No associated systemic symptoms reported. Female patient, age 18–29. The affected area is the leg and arm. Texture is reported as fluid-filled. The patient reported no relevant symptoms from the lesion. Reported duration is about one day. The photograph was taken at a distance:
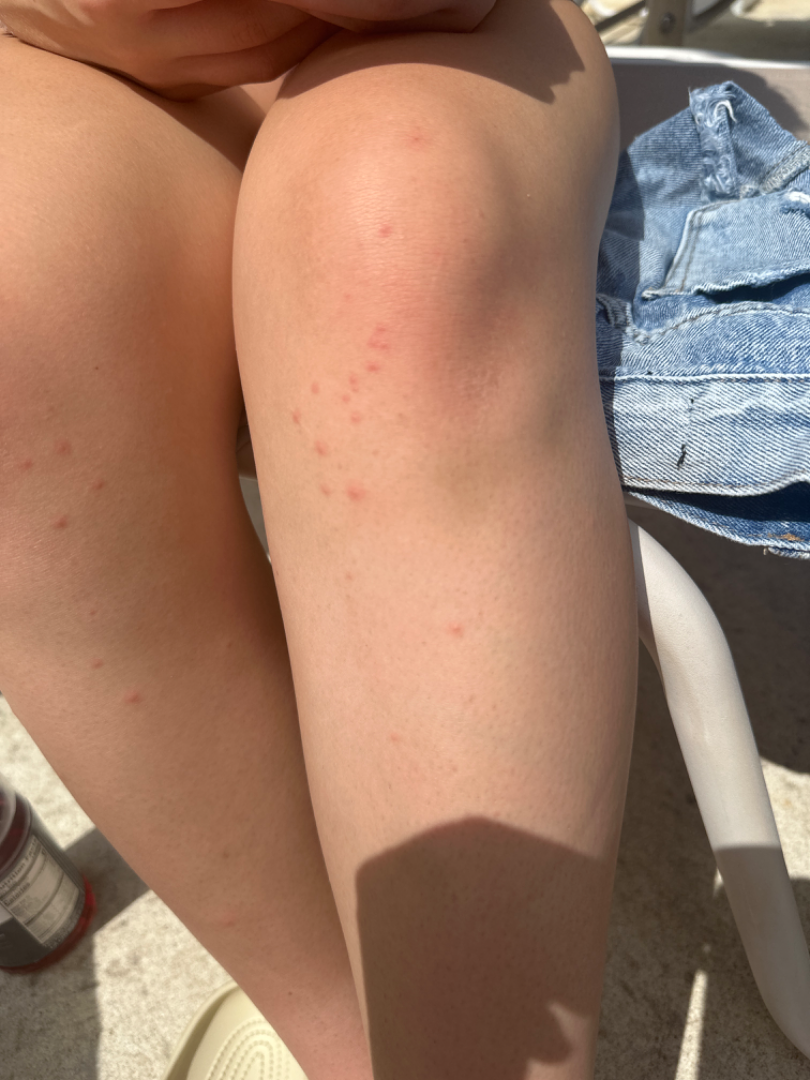diagnostic considerations = one reviewing dermatologist: in keeping with Folliculitis.